A male subject in their mid- to late 80s or older; the patient was assessed as skin type III; a dermatoscopic image of a skin lesion: 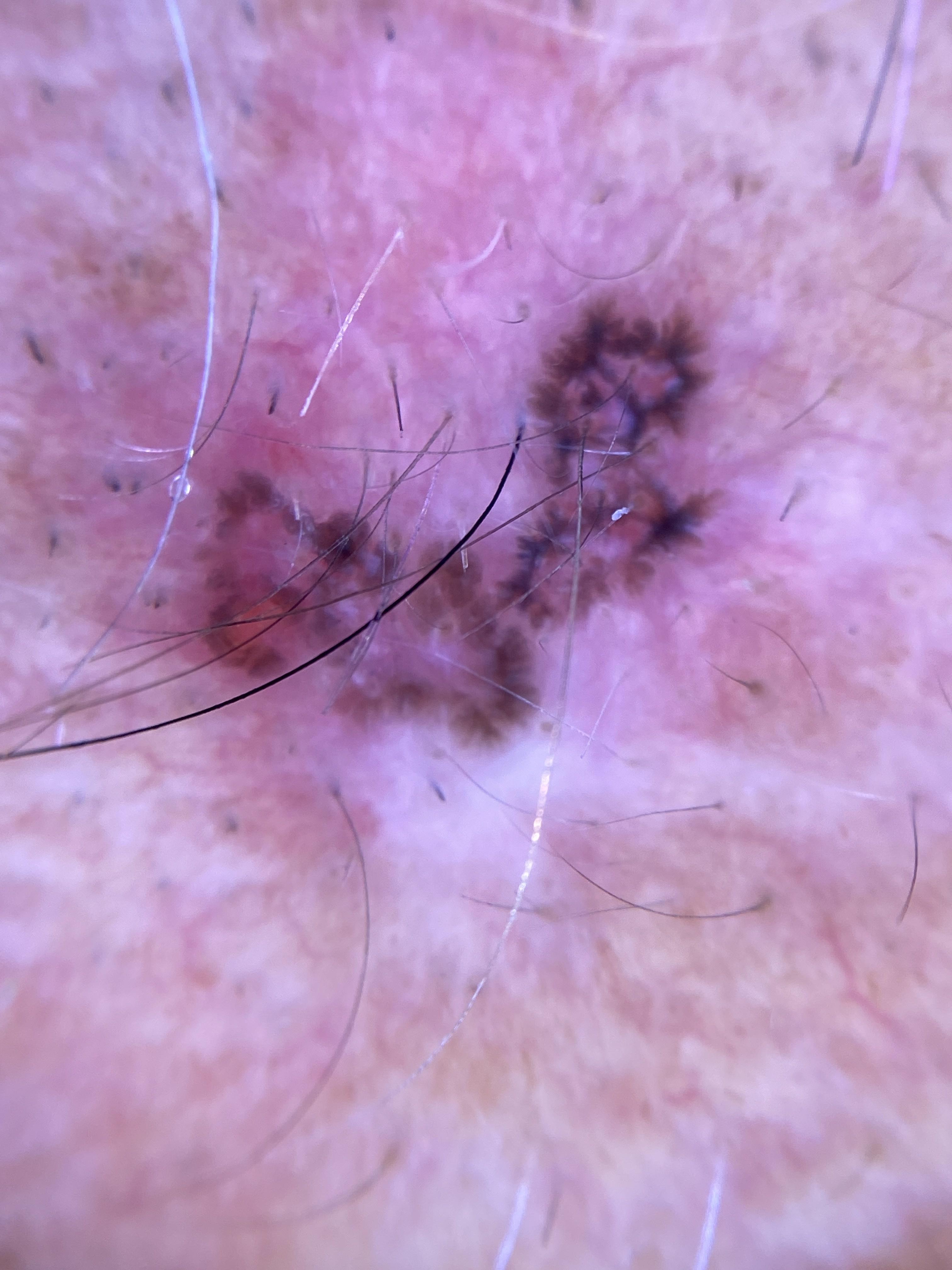<lesion>
  <lesion_location>
    <region>the head or neck</region>
  </lesion_location>
  <diagnosis>
    <name>Basal cell carcinoma</name>
    <malignancy>malignant</malignancy>
    <confirmation>histopathology</confirmation>
    <lineage>adnexal</lineage>
  </diagnosis>
</lesion>